Dermoscopy of a skin lesion. The patient is male.
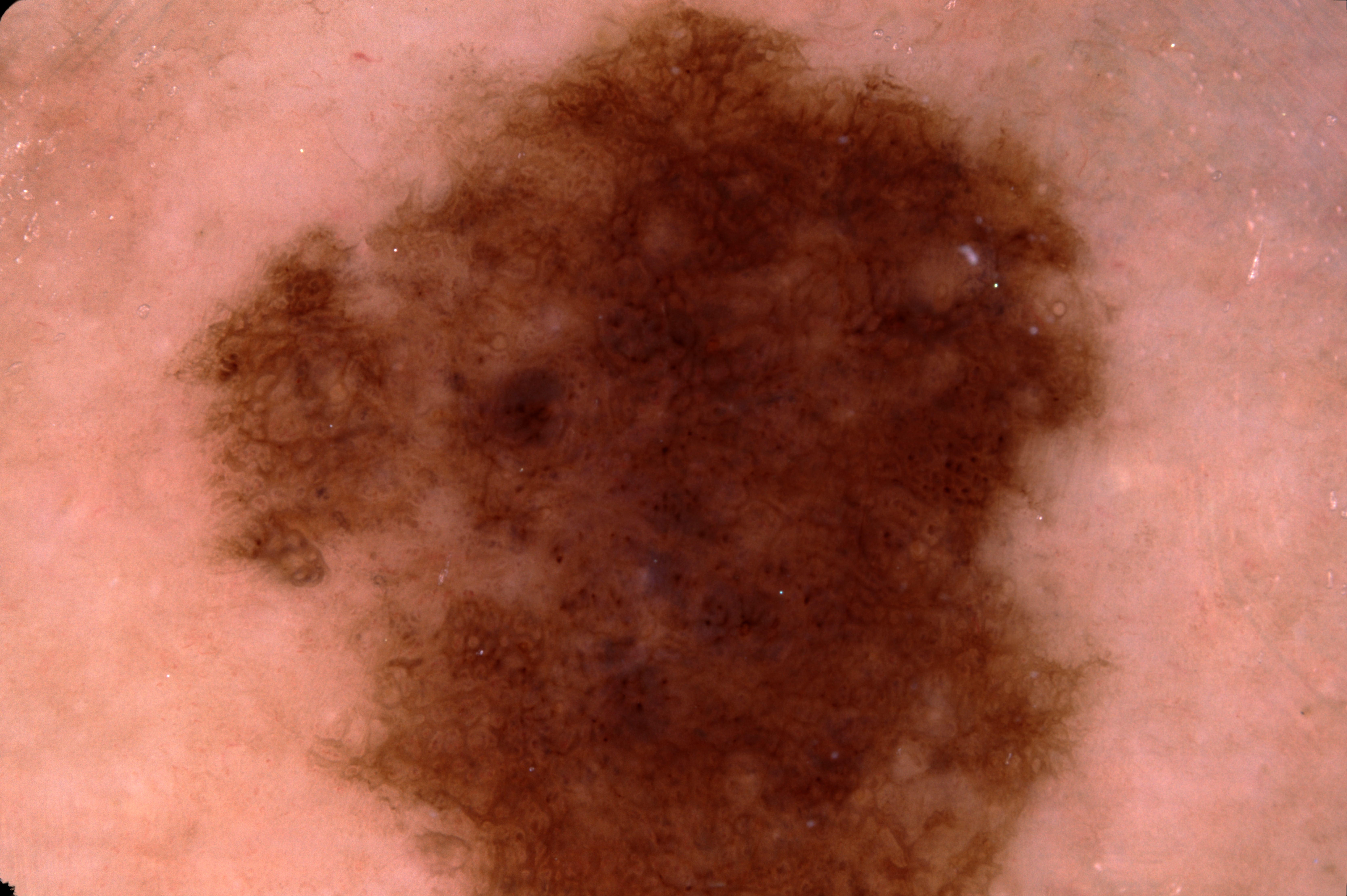The lesion spans 187/0/1122/895. A prominent lesion filling much of the field. The lesion runs off the edge of the field of view. Dermoscopic assessment notes pigment network; no negative network, milia-like cysts, or streaks. Consistent with a melanocytic nevus, a benign lesion.